The patient reported no relevant symptoms from the lesion · the affected area is the leg, front of the torso, arm and back of the torso · the photograph was taken at an angle · the patient reported no systemic symptoms · the condition has been present for one to four weeks · the patient described the issue as a rash · texture is reported as rough or flaky and raised or bumpy — 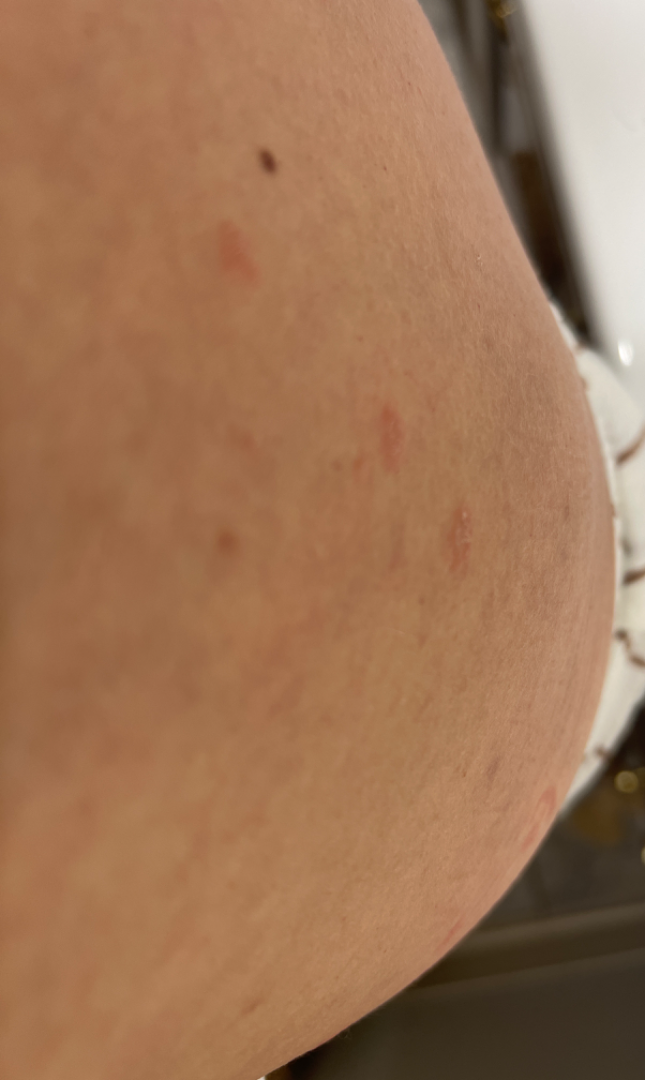assessment = indeterminate.